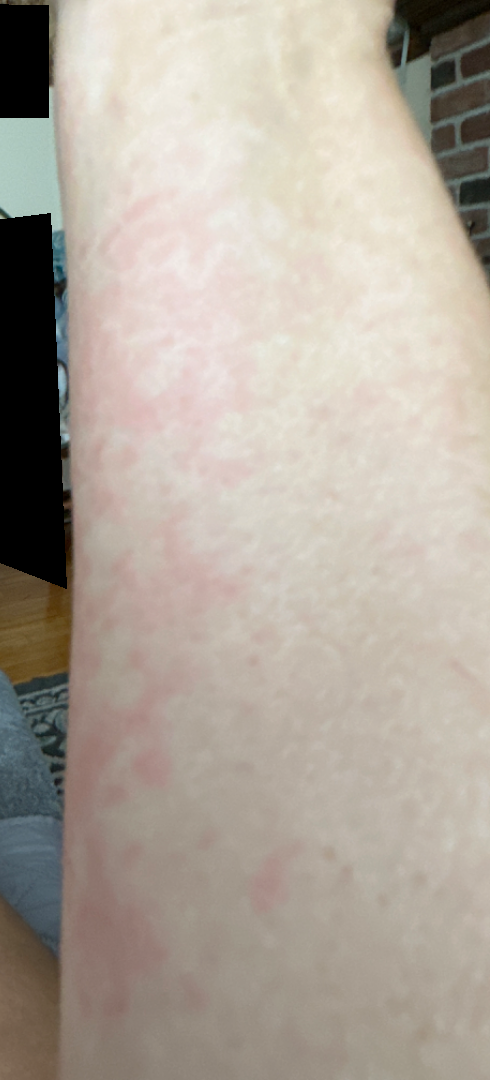On photographic review: most consistent with Urticaria.